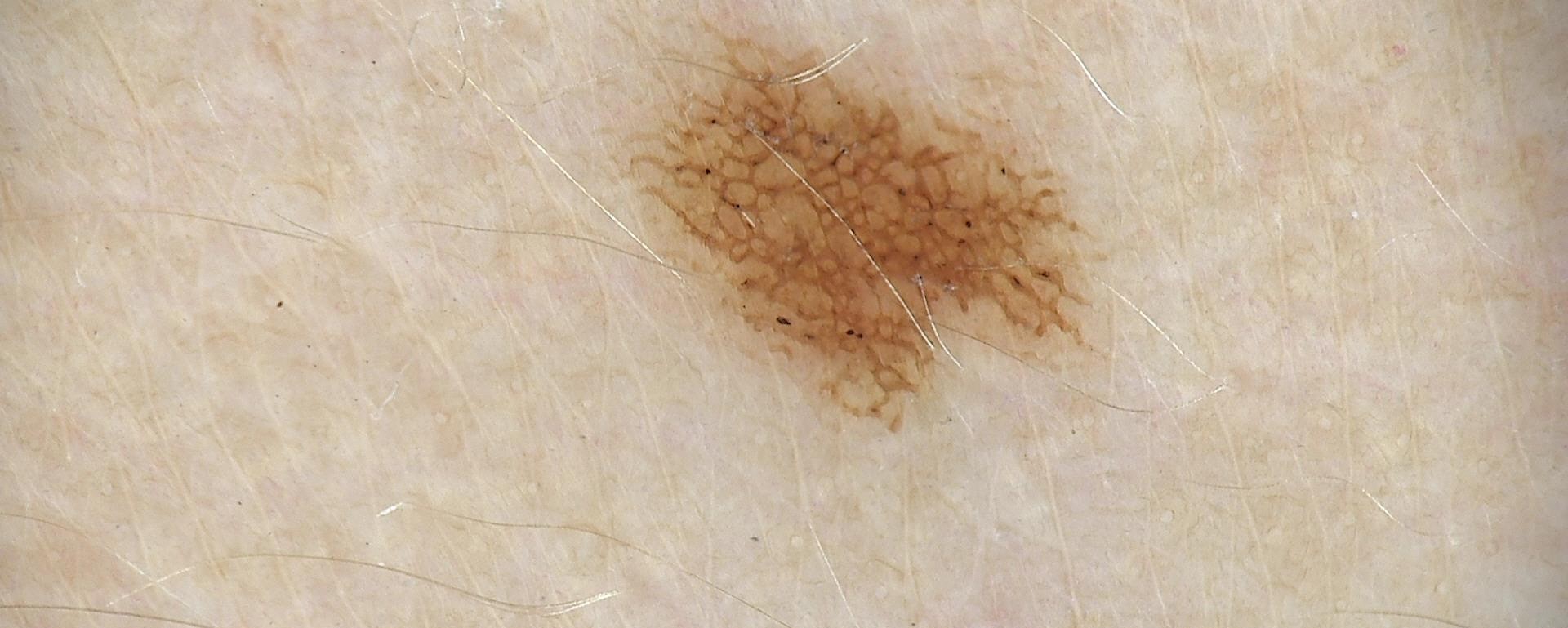{"diagnosis": {"name": "dysplastic junctional nevus", "code": "jd", "malignancy": "benign", "super_class": "melanocytic", "confirmation": "expert consensus"}}